Symptoms reported: itching; this is a close-up image; no constitutional symptoms were reported; the lesion involves the back of the torso and front of the torso: 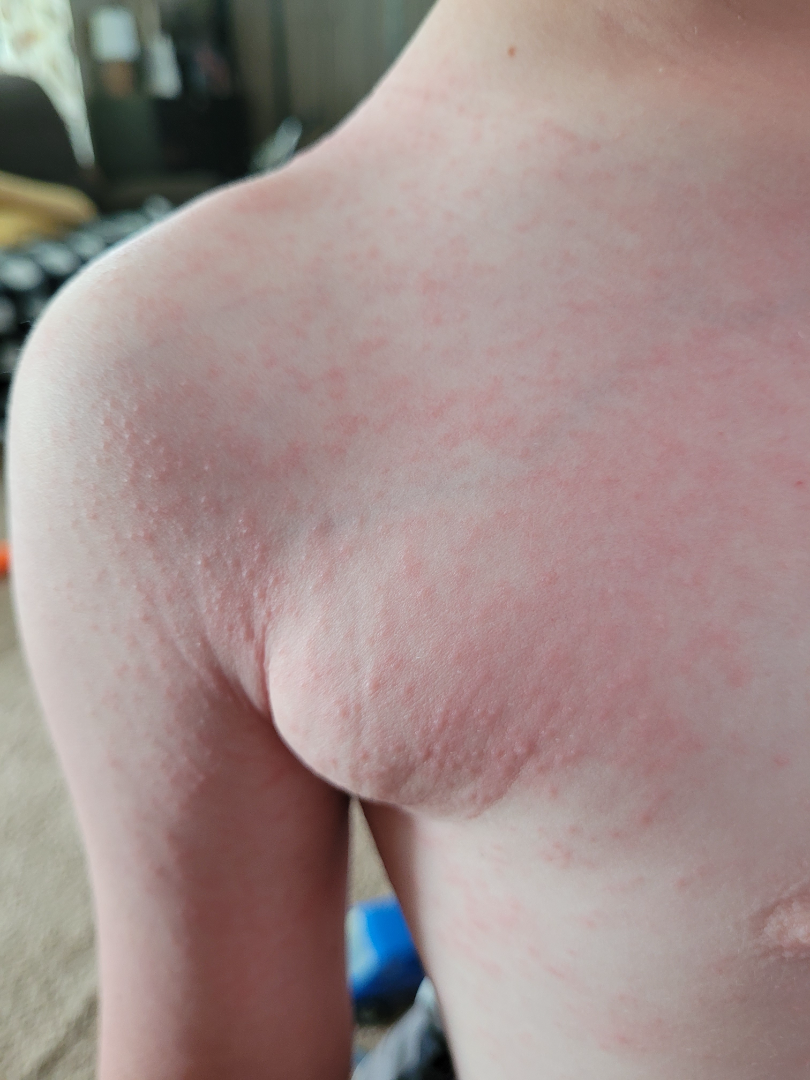  differential:
    leading:
      - Viral Exanthem
    considered:
      - Drug Rash
    unlikely:
      - Insect Bite